Reported duration is about one day; the patient notes the lesion is flat and raised or bumpy; the photo was captured at a distance; the subject is a female aged 30–39 — 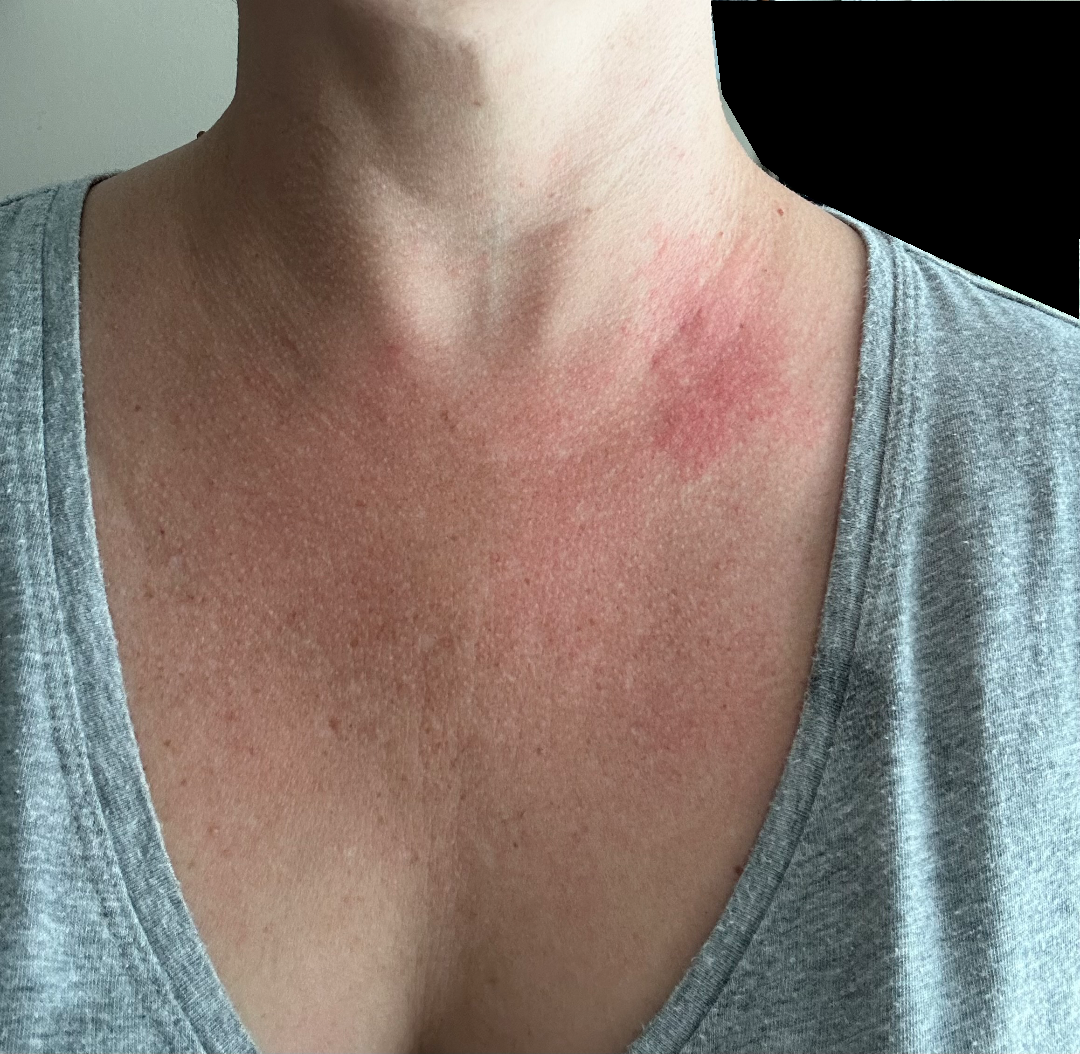Review:
Berloque dermatitis, Allergic Contact Dermatitis and Irritant Contact Dermatitis were each considered, in no particular order.